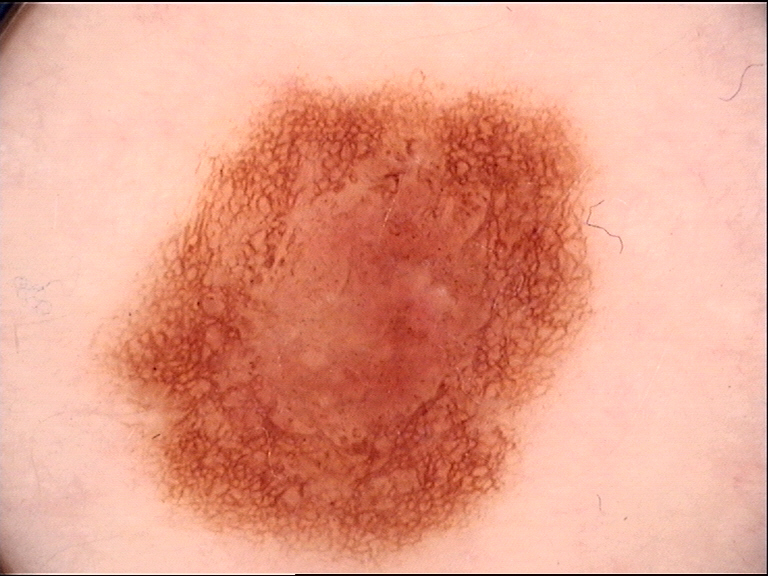A dermatoscopic image of a skin lesion.
Classified as a benign lesion — a dysplastic compound nevus.